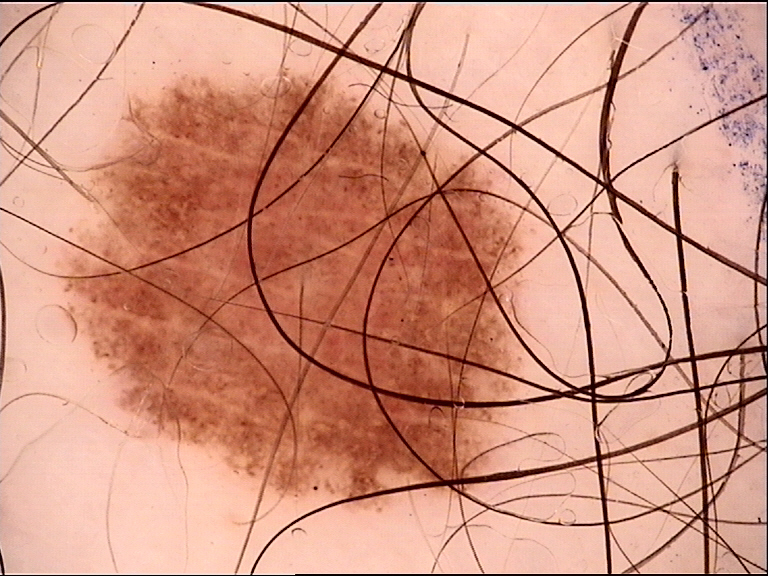<lesion>
<diagnosis>
<name>dysplastic junctional nevus</name>
<code>jd</code>
<malignancy>benign</malignancy>
<super_class>melanocytic</super_class>
<confirmation>expert consensus</confirmation>
</diagnosis>
</lesion>